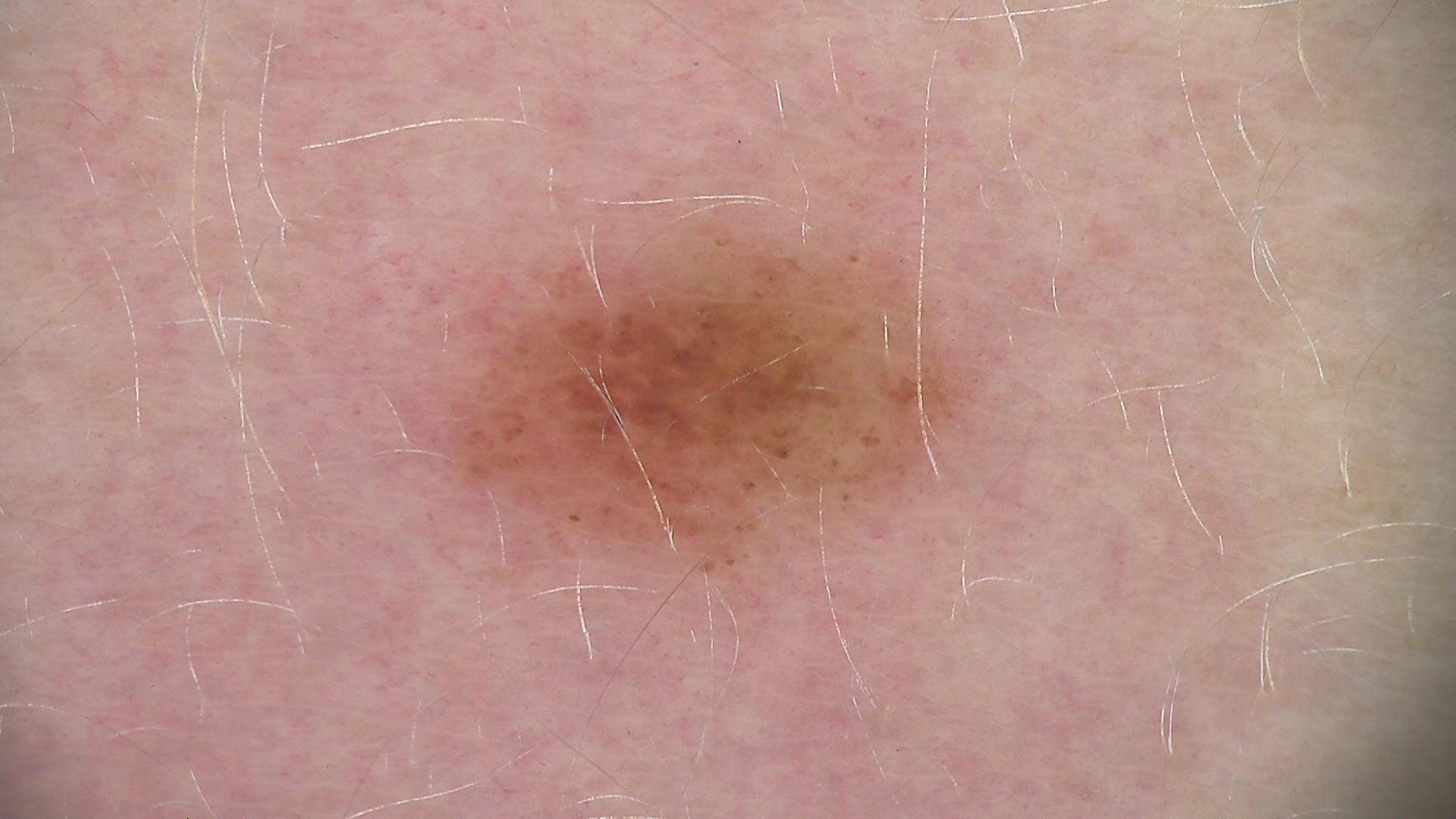Labeled as a dysplastic junctional nevus.